A female subject aged around 45 · a skin lesion imaged with a dermatoscope:
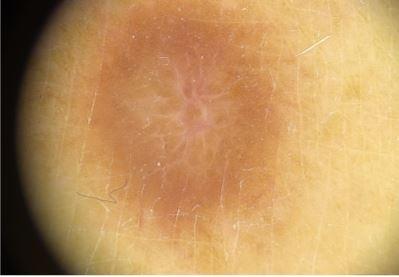Located on a lower extremity. The diagnostic impression was a benign lesion — a dermatofibroma.